A female subject aged around 55; a skin lesion imaged with a dermatoscope — 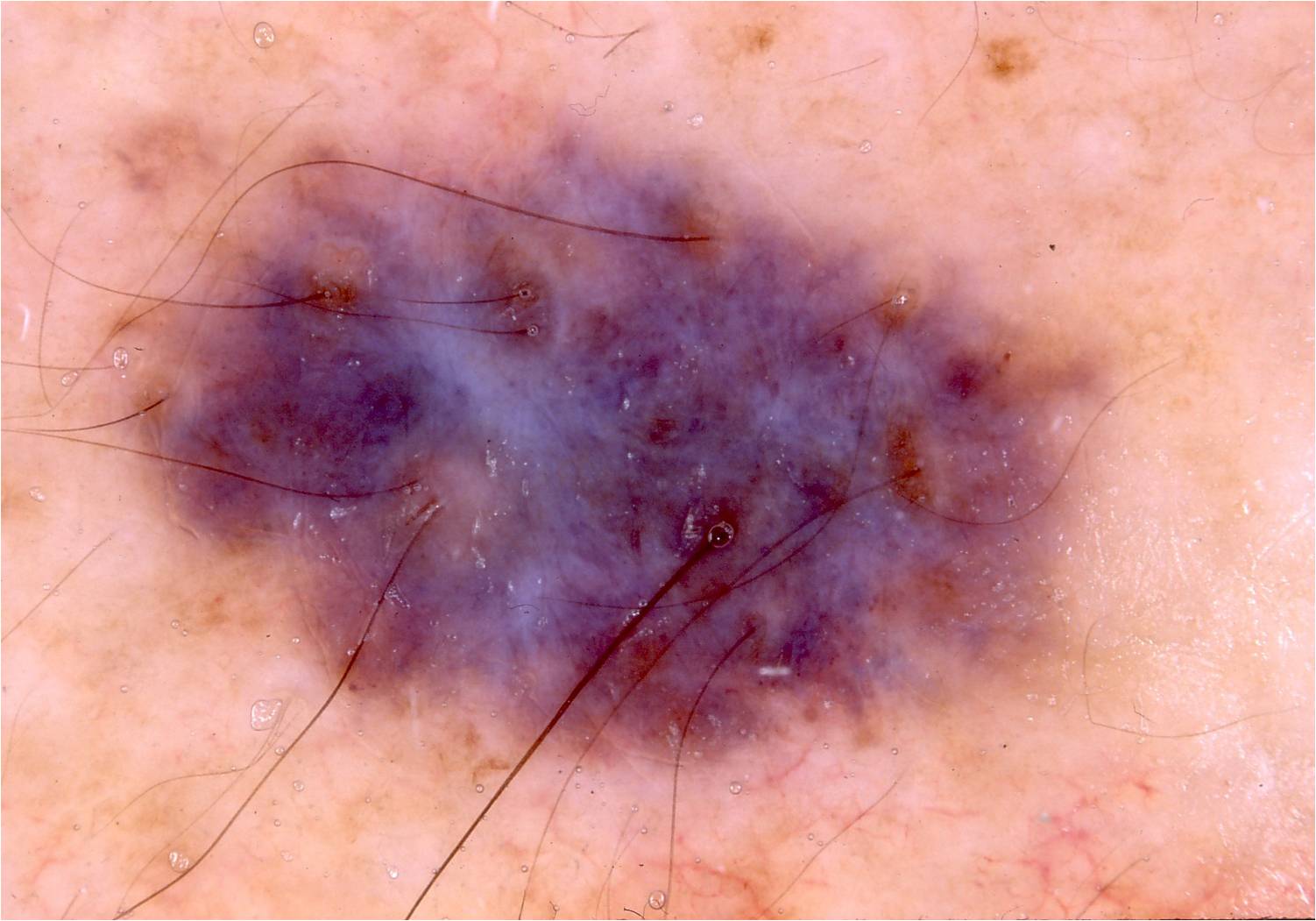<record>
  <dermoscopic_features>
    <present>globules</present>
    <absent>streaks, negative network, milia-like cysts, pigment network</absent>
  </dermoscopic_features>
  <lesion_location>
    <bbox_xyxy>25, 60, 1143, 797</bbox_xyxy>
  </lesion_location>
  <diagnosis>
    <name>melanocytic nevus</name>
    <malignancy>benign</malignancy>
    <lineage>melanocytic</lineage>
    <provenance>clinical</provenance>
  </diagnosis>
</record>